Located on the arm. This is a close-up image. Fitzpatrick phototype I. The lesion is described as raised or bumpy. Self-categorized by the patient as a rash: 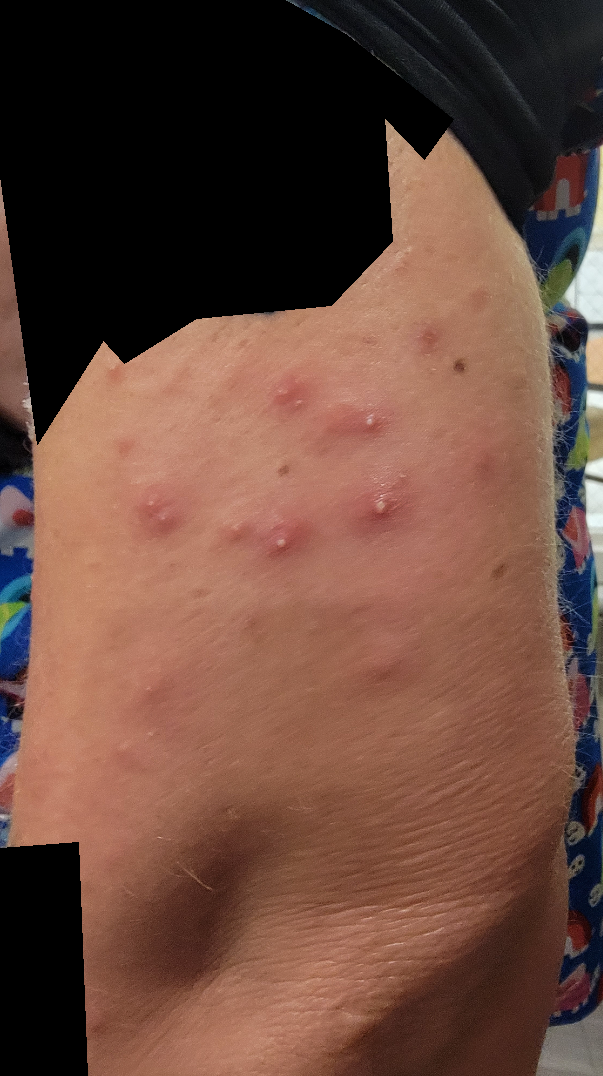Folliculitis (leading); Miliaria (considered); Drug Rash (remote).